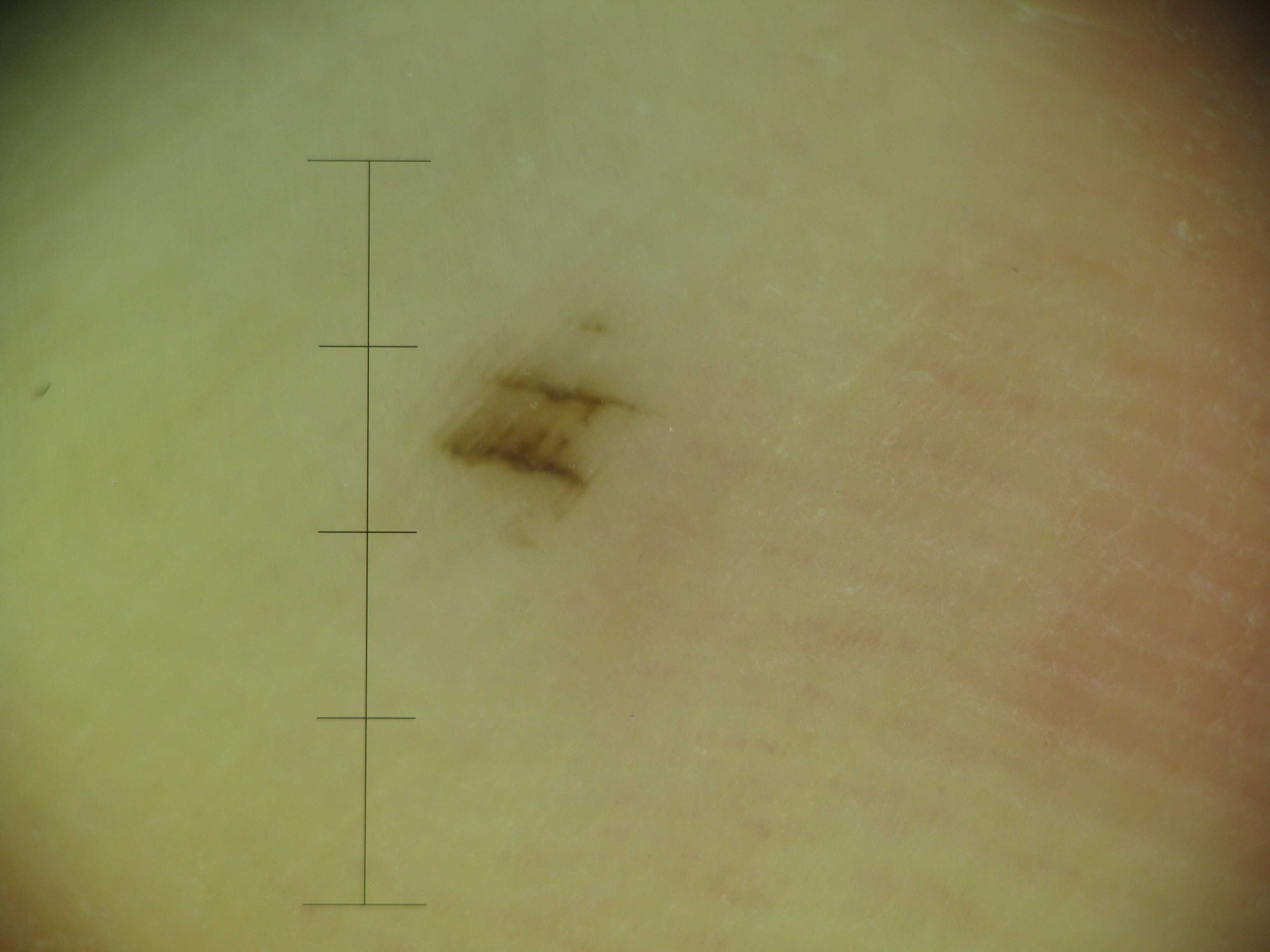Dermoscopy of a skin lesion. Consistent with a banal lesion — an acral junctional nevus.